A skin lesion imaged with a dermatoscope.
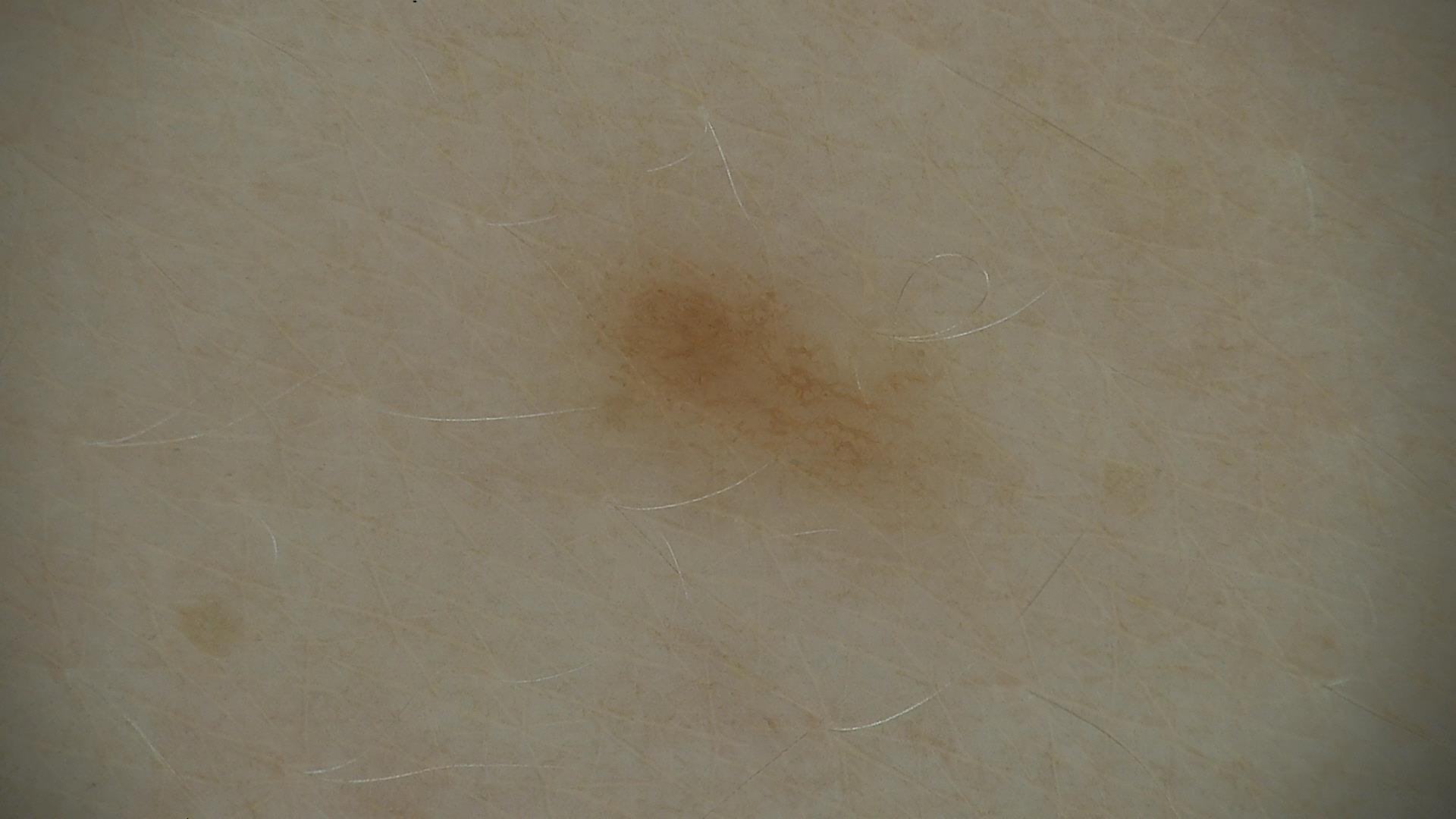Classified as a benign lesion — a dysplastic junctional nevus.